A dermoscopic image of a skin lesion:
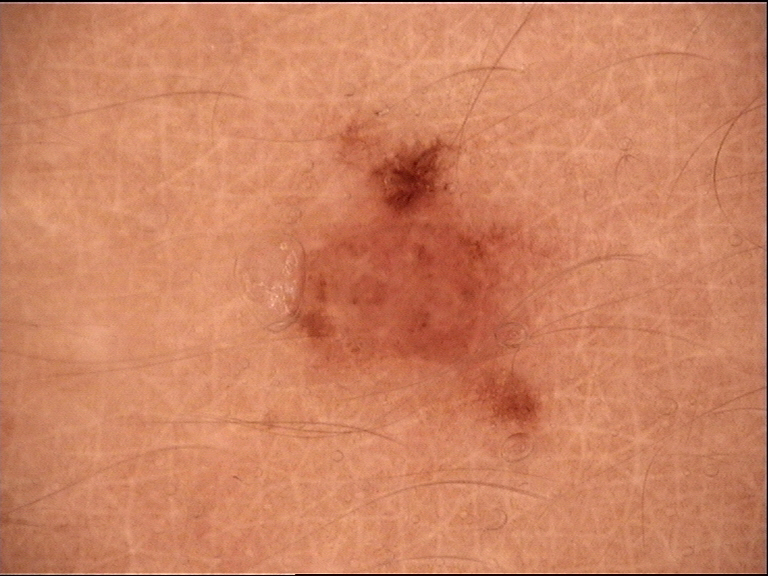label = dysplastic compound nevus (expert consensus)